Male patient, age 40–49 · close-up view · located on the front of the torso and back of the torso:
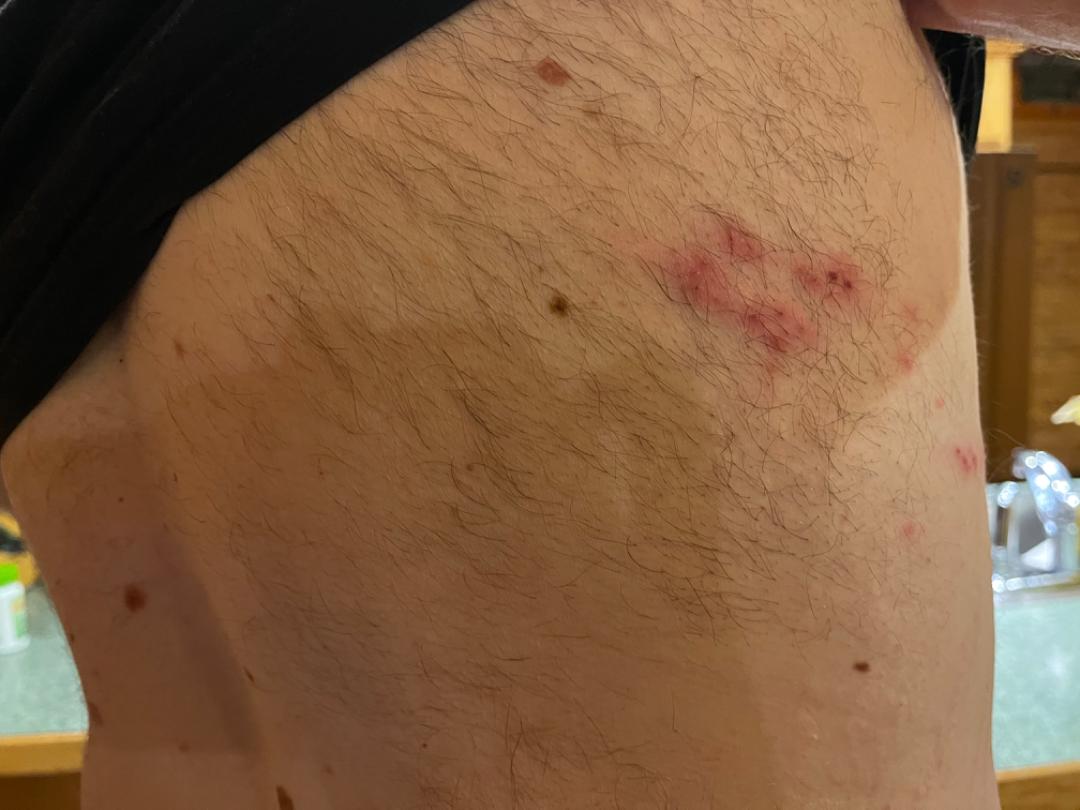Fitzpatrick phototype II; human graders estimated MST 2 or 3.
Texture is reported as raised or bumpy.
Present for less than one week.
The contributor reports burning, pain, bothersome appearance and itching.
Self-categorized by the patient as a rash.
The patient reported no systemic symptoms.
Reviewed remotely by one dermatologist: favoring Herpes Zoster; also on the differential is Eczema.